A dermoscopic photograph of a skin lesion.
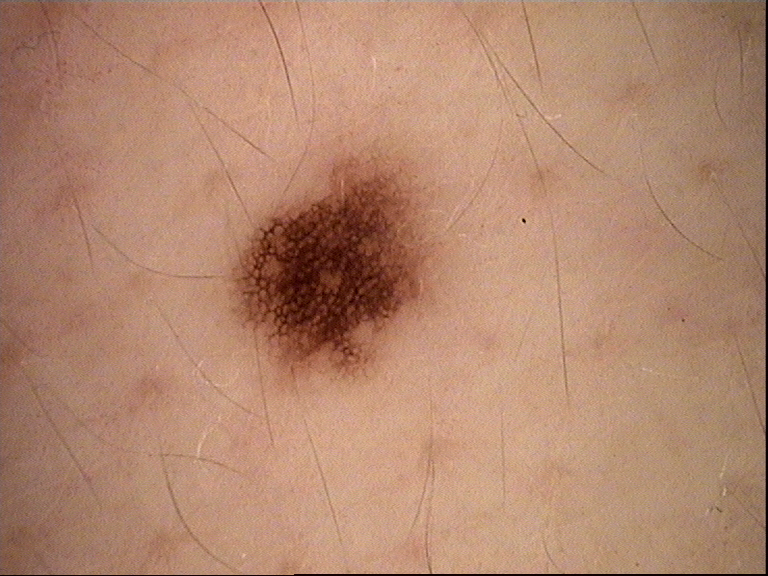Diagnosed as a banal lesion — a junctional nevus.